A dermatoscopic image of a skin lesion:
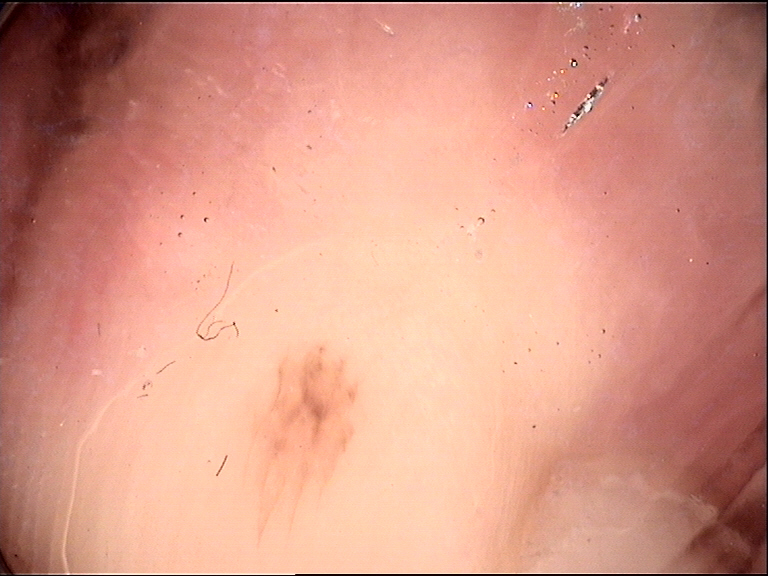• diagnostic label — acral dysplastic junctional nevus (expert consensus)